A dermoscopic image of a skin lesion. A male subject aged approximately 40 — 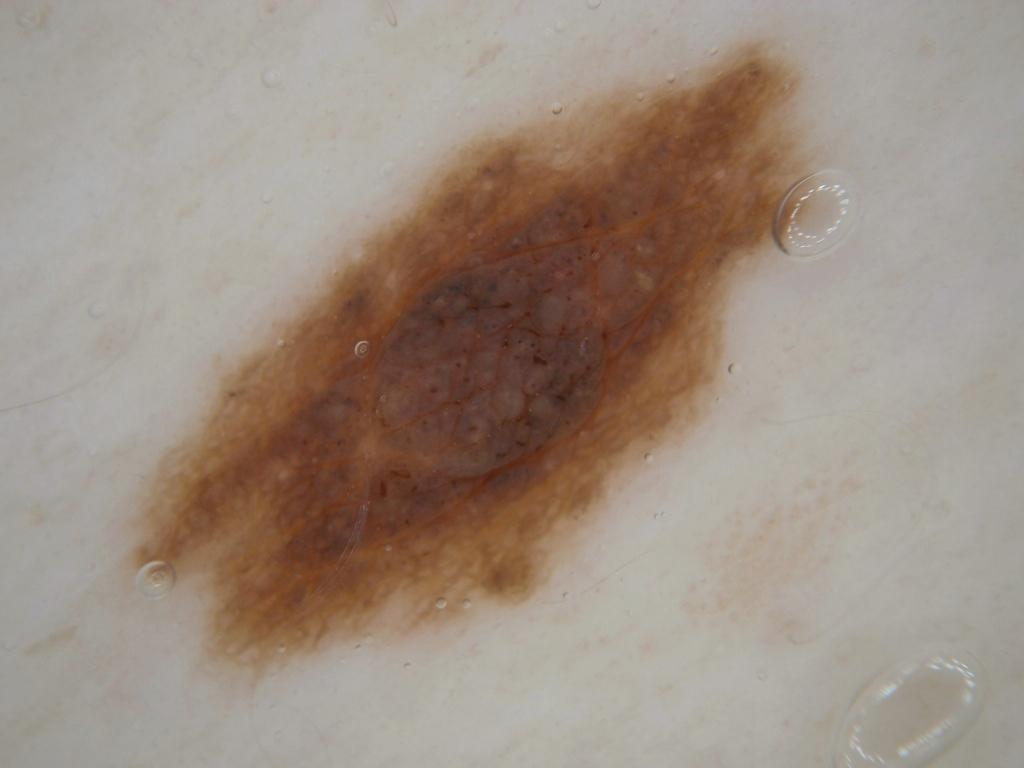Summary: The dermoscopic pattern shows pigment network and globules. The lesion is located at 122, 40, 815, 678. Conclusion: The lesion was assessed as a melanocytic nevus, a benign skin lesion.